Female patient, age 30–39 · the photograph was taken at an angle · the lesion involves the leg and top or side of the foot:
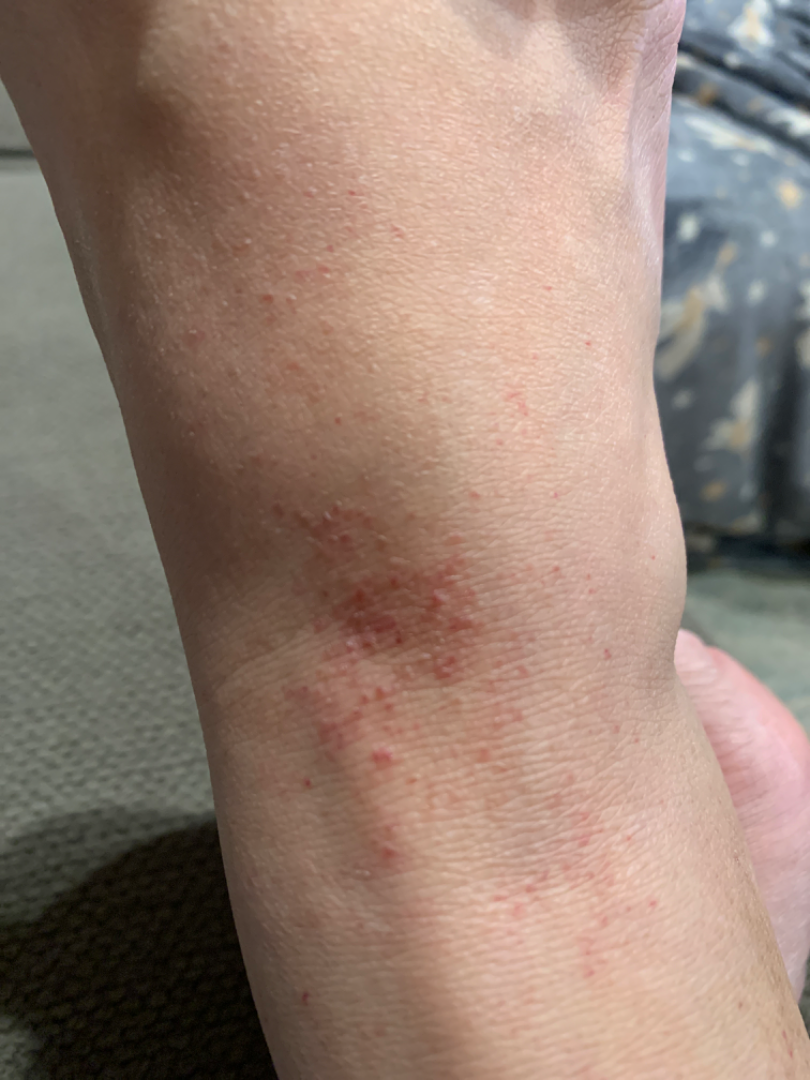Assessment:
On photographic review: Pigmented purpuric eruption (35%); Lichen Simplex Chronicus (21%); Eczema (20%); Leukocytoclastic Vasculitis (13%); Allergic Contact Dermatitis (11%).